A male subject approximately 70 years of age.
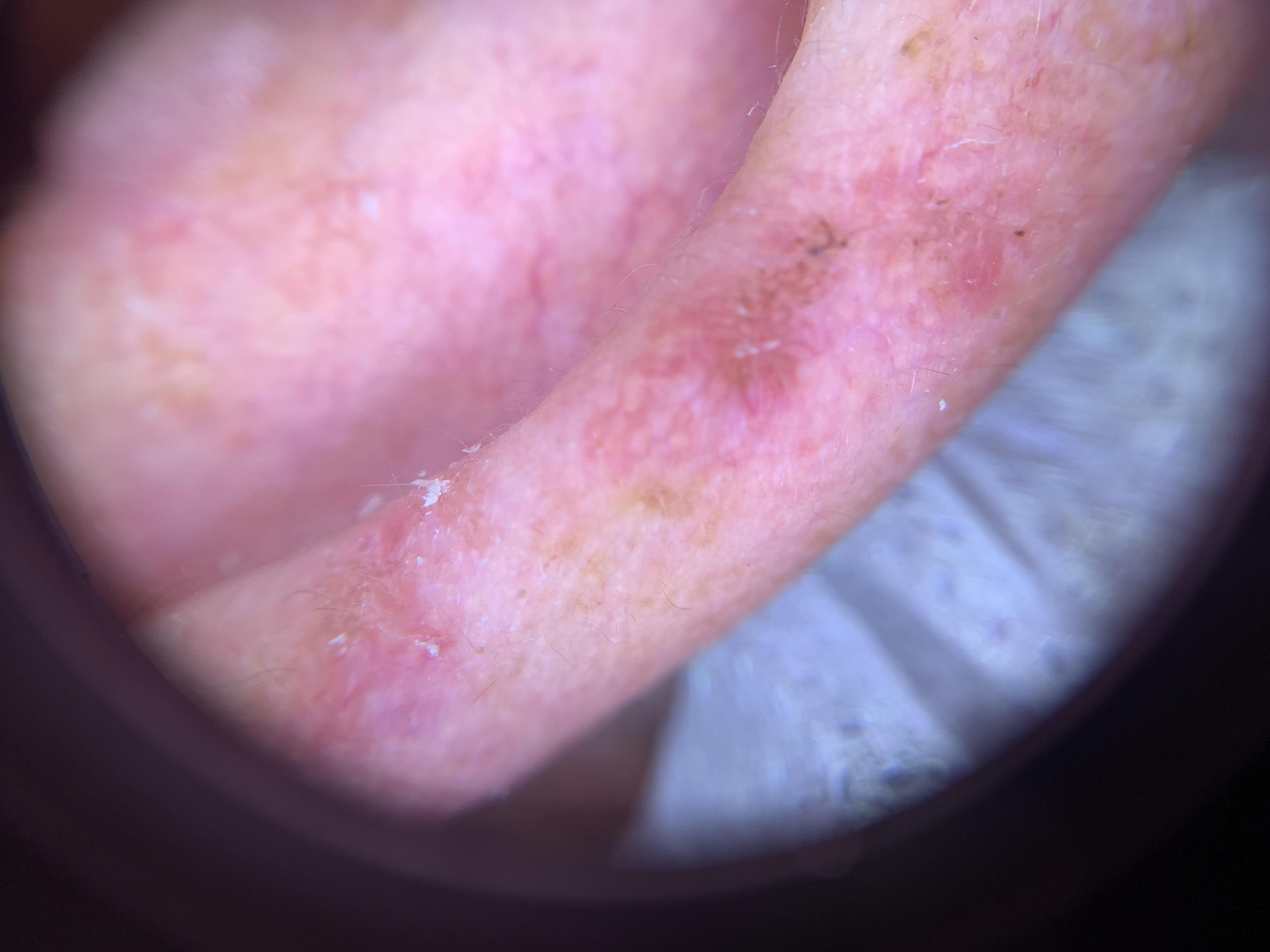{
  "lesion_location": {
    "region": "the head or neck"
  },
  "diagnosis": {
    "name": "Basal cell carcinoma",
    "malignancy": "malignant",
    "confirmation": "histopathology",
    "lineage": "adnexal"
  }
}